A dermoscopic photograph of a skin lesion.
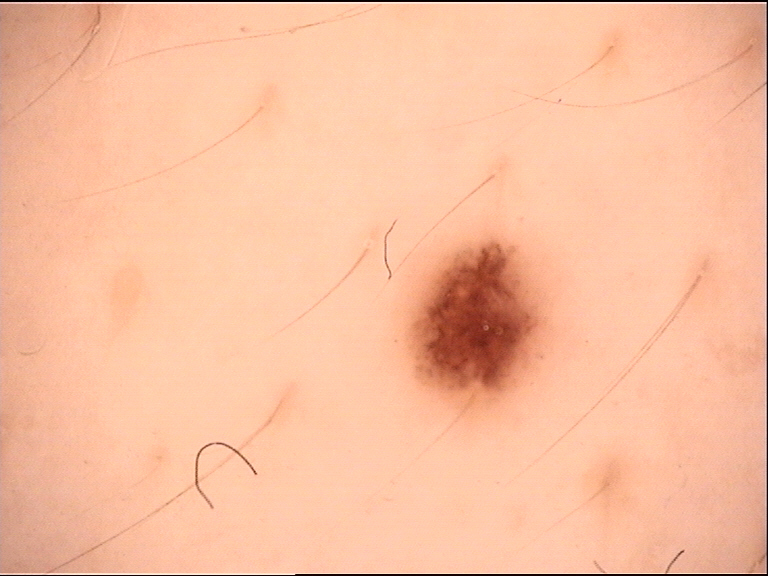Consistent with a dysplastic junctional nevus.